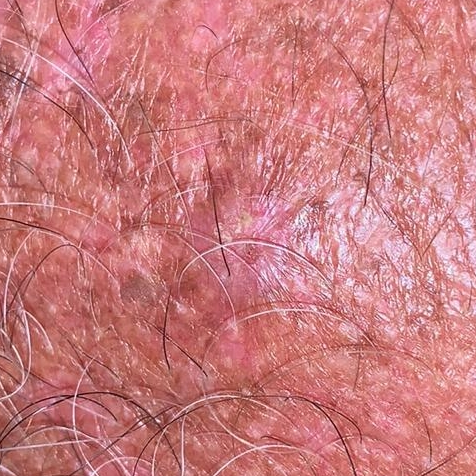Findings: A clinical photograph of a skin lesion. The lesion involves the chest. By the patient's account, the lesion is elevated and itches. Conclusion: The biopsy diagnosis was an actinic keratosis.